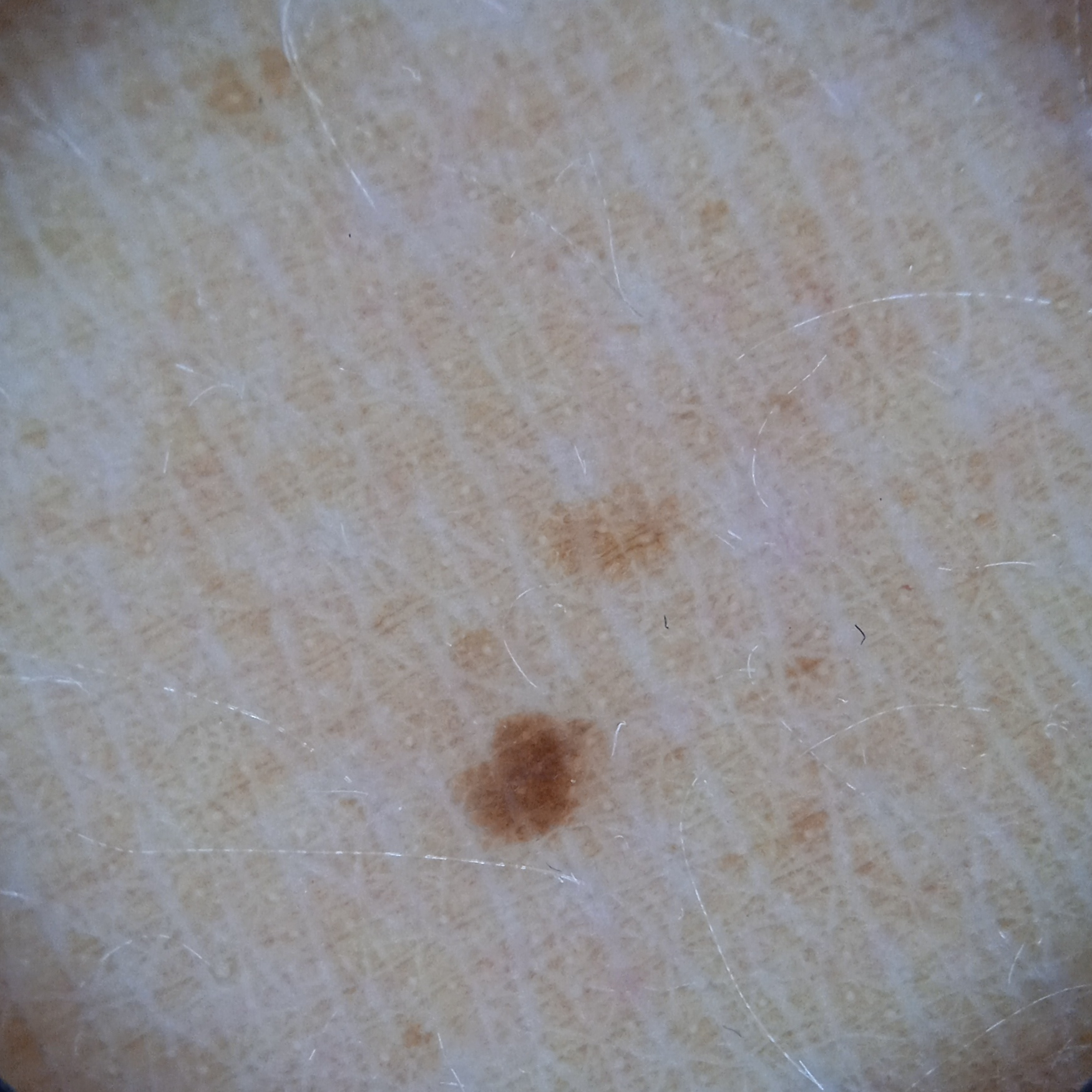Acquired for a research image collection, with no referral diagnosis. On a questionnaire the patient reported a history of sunbed use. A dermoscopic image of a skin lesion. The lesion involves the back. Measuring roughly 1.8 mm. Reviewed by four dermatologists, the consensus diagnosis was a melanocytic nevus; agreement among the reviewers was unanimous; the reviewers were fairly confident.